A dermoscopic close-up of a skin lesion; the patient was assessed as skin type II.
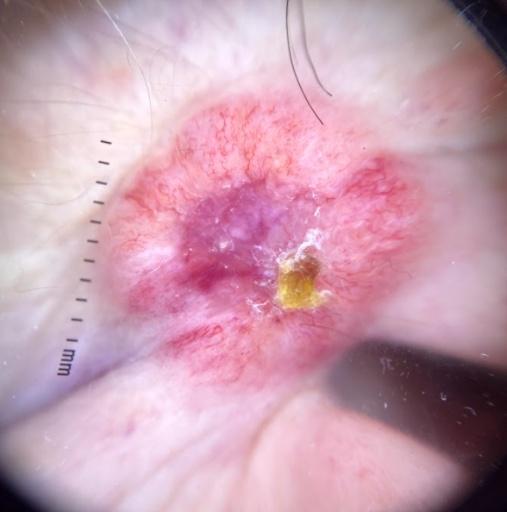Conclusion:
Histopathological examination showed a malignant, adnexal lesion — a basal cell carcinoma.